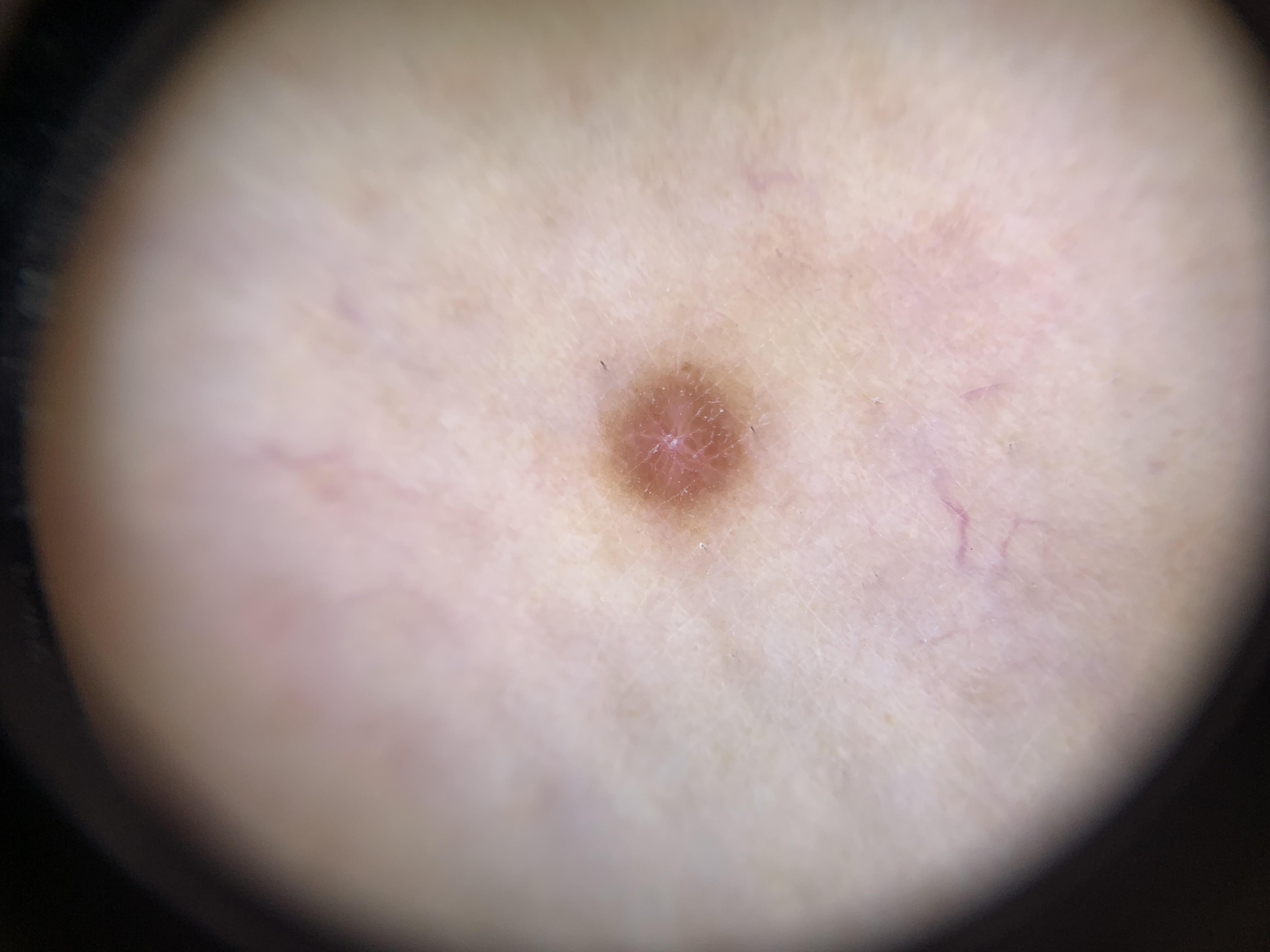A male patient approximately 40 years of age.
Located on a lower extremity.
Clinically diagnosed as a dermatofibroma.